This is a close-up image. The lesion involves the leg. The contributor is a male aged 50–59 — 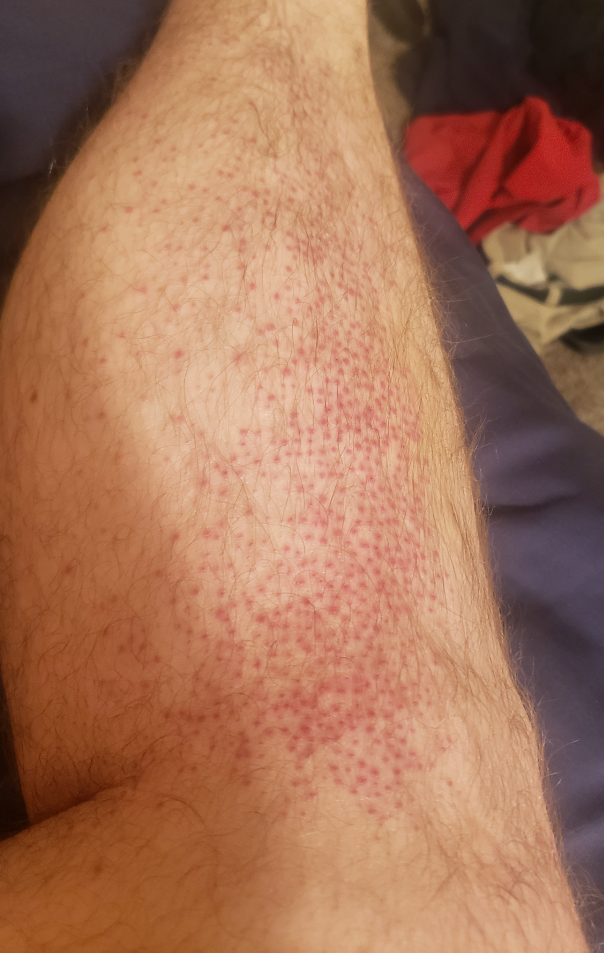The primary impression is Folliculitis.